An image taken at an angle · the patient is 50–59, female · the lesion involves the head or neck and arm:
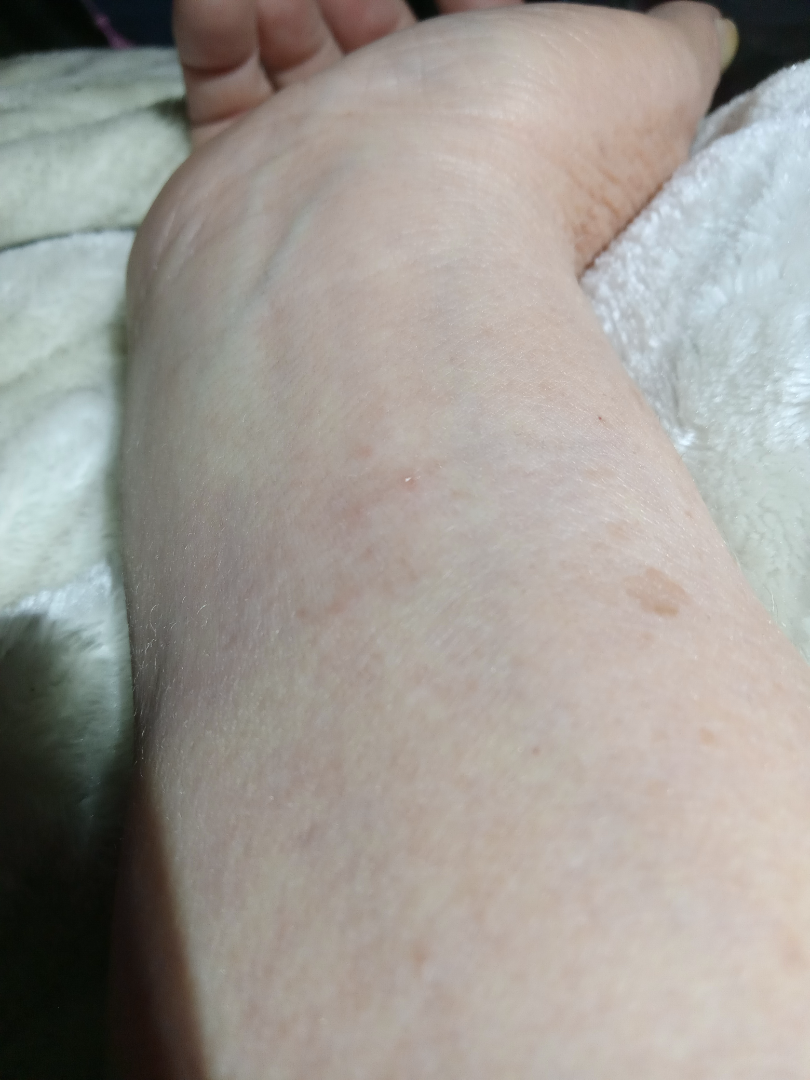The contributor reports the condition has been present for less than one week.
The contributor reports the lesion is raised or bumpy.
The contributor reports associated fatigue and joint pain.
The contributor reports burning and itching.
Self-categorized by the patient as a rash.
The reviewing dermatologist's impression was: the differential is split between Eczema, Hypersensitivity and Allergic Contact Dermatitis.